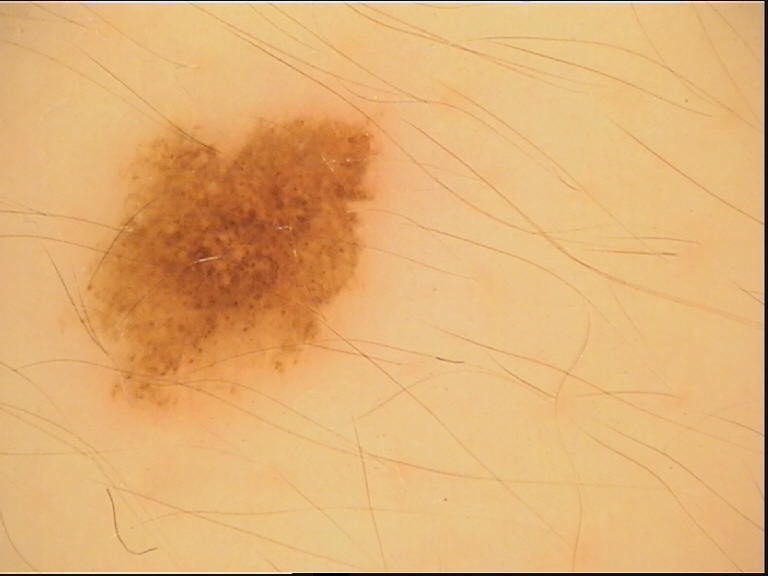Labeled as a benign lesion — a dysplastic compound nevus.